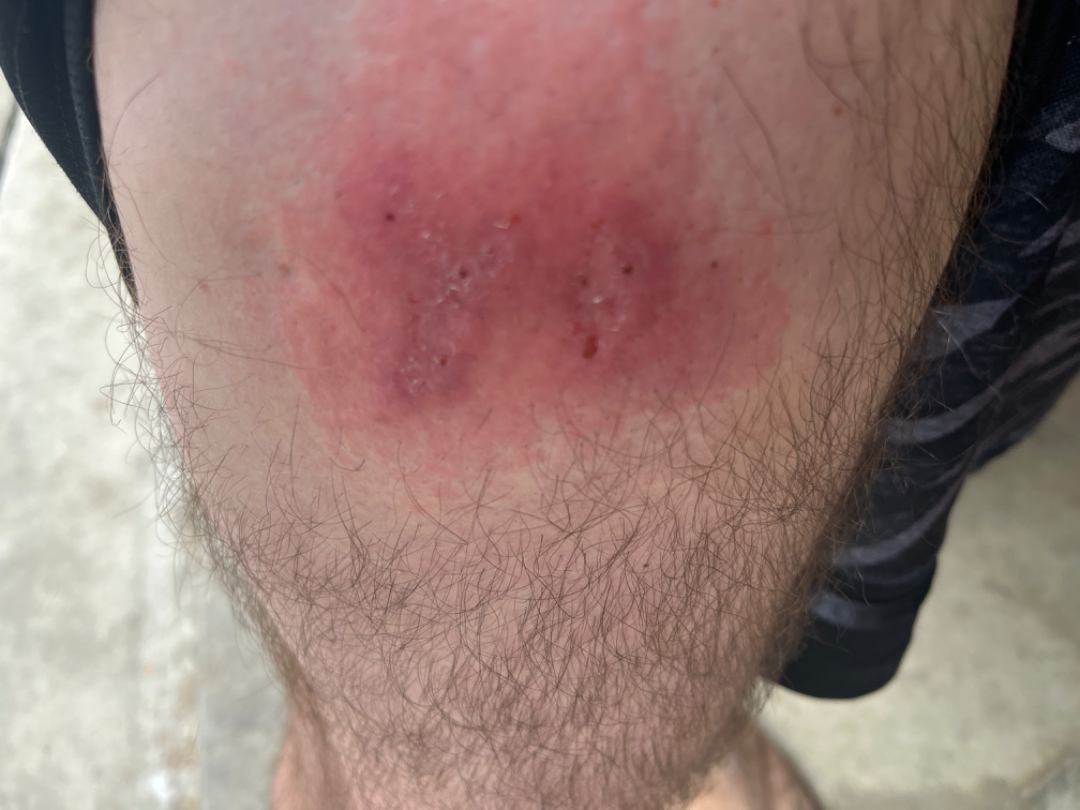The condition could not be reliably identified from the image.